This image was taken at a distance. Symptoms reported: darkening, pain, itching, bothersome appearance, bleeding, enlargement and burning. Present for one to four weeks. Texture is reported as fluid-filled. The affected area is the palm and back of the hand — 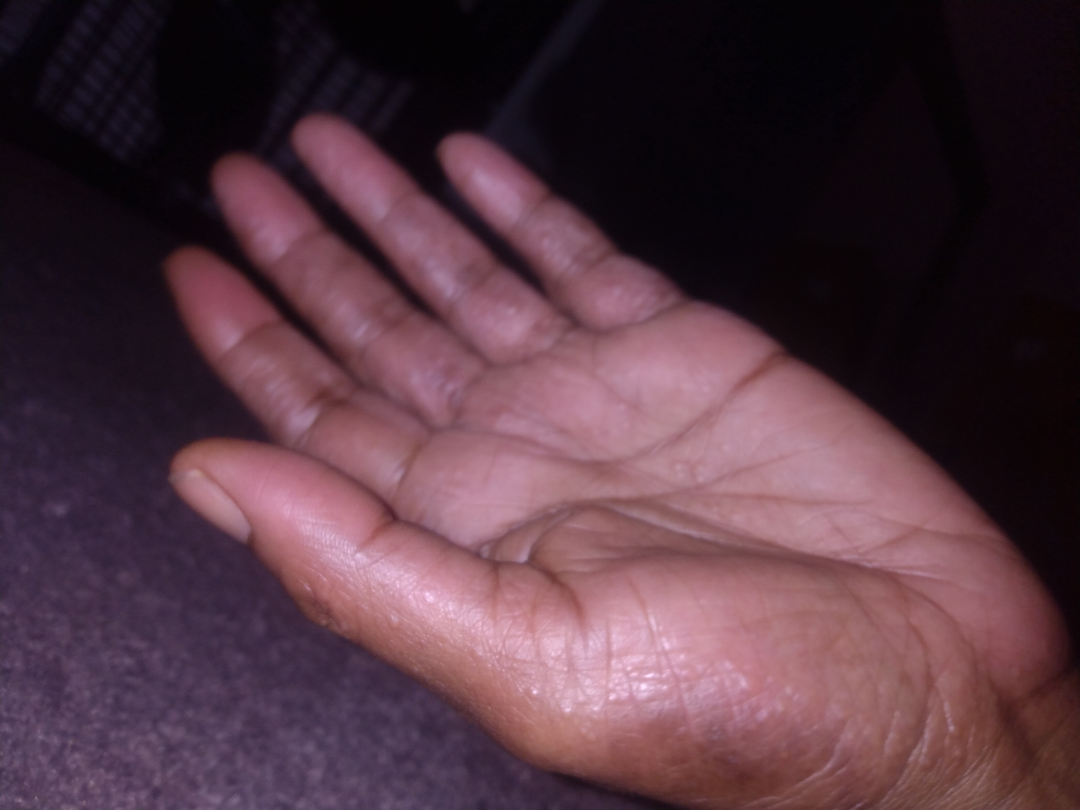On dermatologist assessment of the image: Eczema (weight 0.28); Acral persistent papular mucinosis (weight 0.22); Cutaneous sarcoidosis (weight 0.22); Allergic Contact Dermatitis (weight 0.17); Verruca vulgaris (weight 0.11).